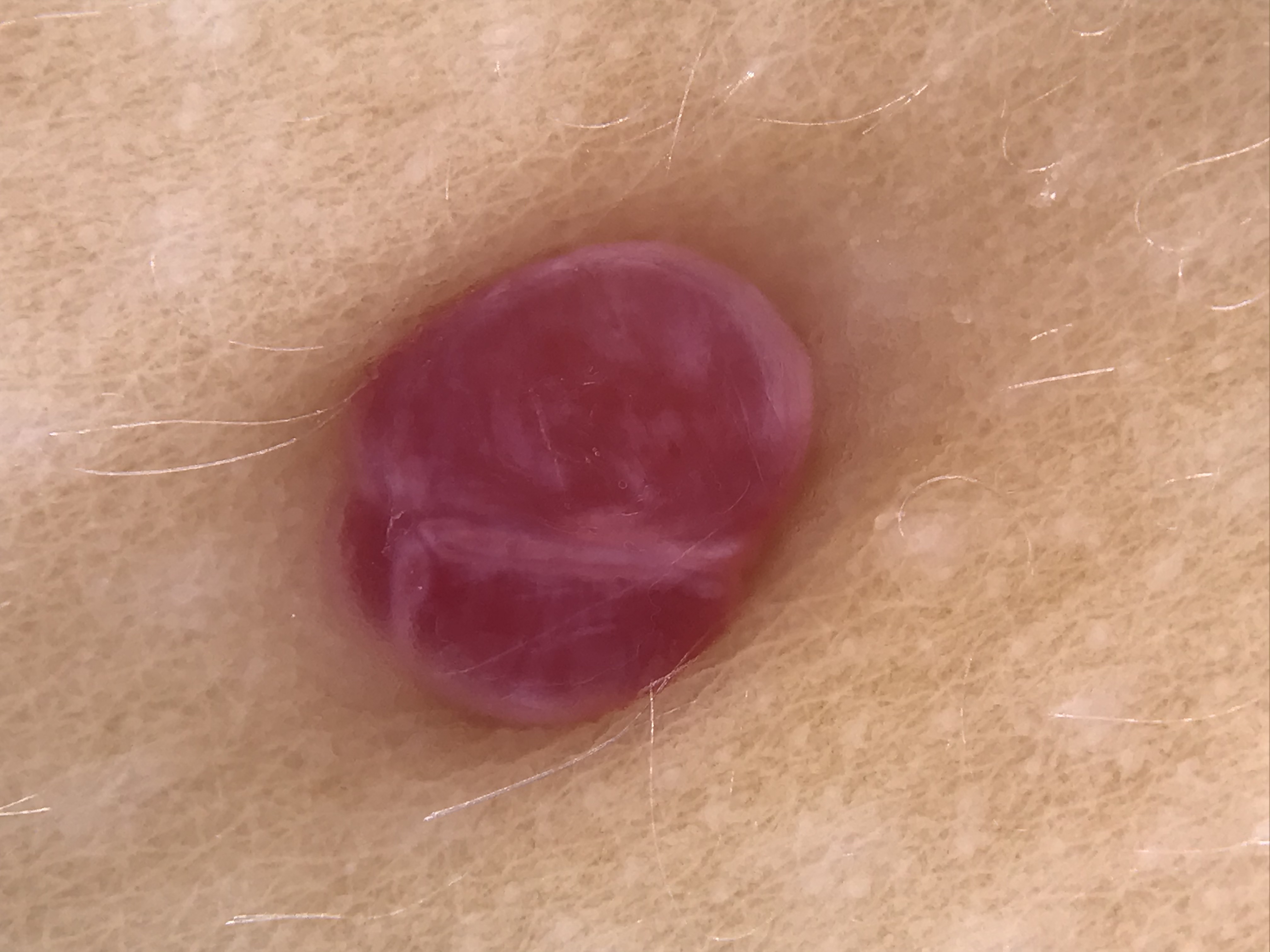– assessment: pyogenic granuloma (expert consensus)